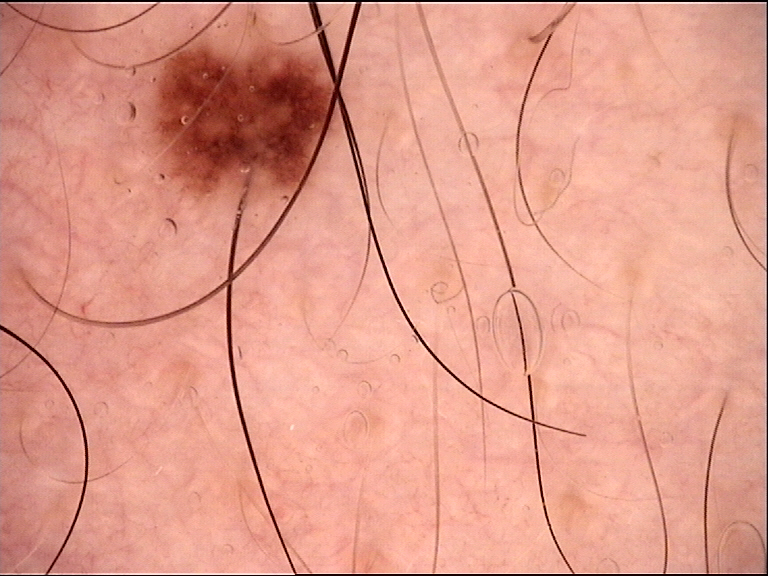Diagnosed as a dysplastic junctional nevus.